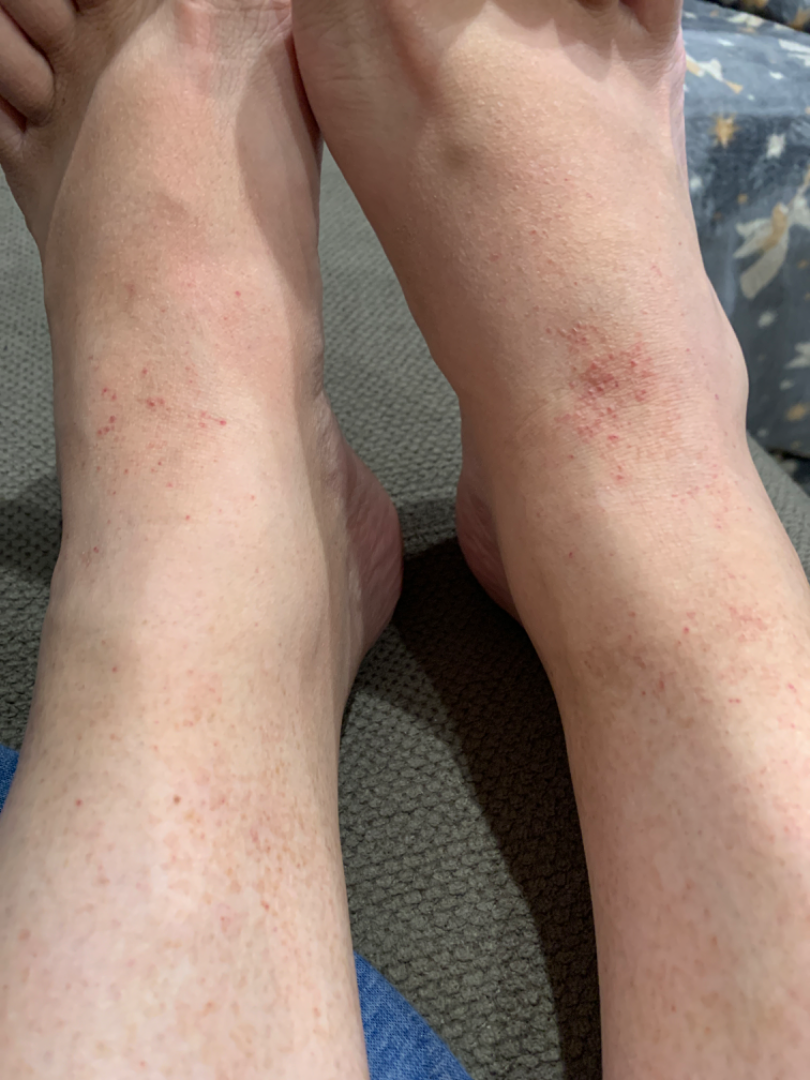Reported lesion symptoms include bothersome appearance. Female patient, age 30–39. No associated systemic symptoms reported. An image taken at a distance. FST II; non-clinician graders estimated a Monk Skin Tone of 3. The lesion involves the leg and top or side of the foot. The patient reports the lesion is raised or bumpy. The condition has been present for less than one week. Most consistent with Pigmented purpuric eruption; an alternative is Lichen Simplex Chronicus; also raised was Eczema; less probable is Leukocytoclastic Vasculitis; a remote consideration is Allergic Contact Dermatitis.